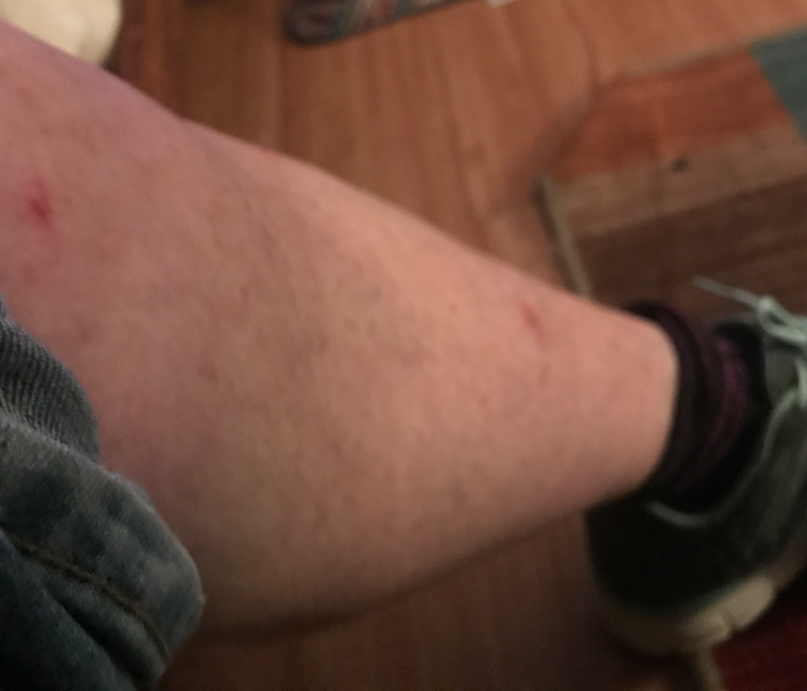Case summary:
- patient's own categorization · a rash
- patient · female, age 50–59
- view · at an angle
- other reported symptoms · none reported
- lesion texture · raised or bumpy
- present for · one to four weeks
- site · front of the torso, back of the hand, arm, back of the torso and head or neck
- symptoms · itching, enlargement, burning, bothersome appearance, bleeding and pain
- differential diagnosis · the impression was split between Folliculitis and Insect Bite